The patient is a female approximately 40 years of age · a dermatoscopic image of a skin lesion:
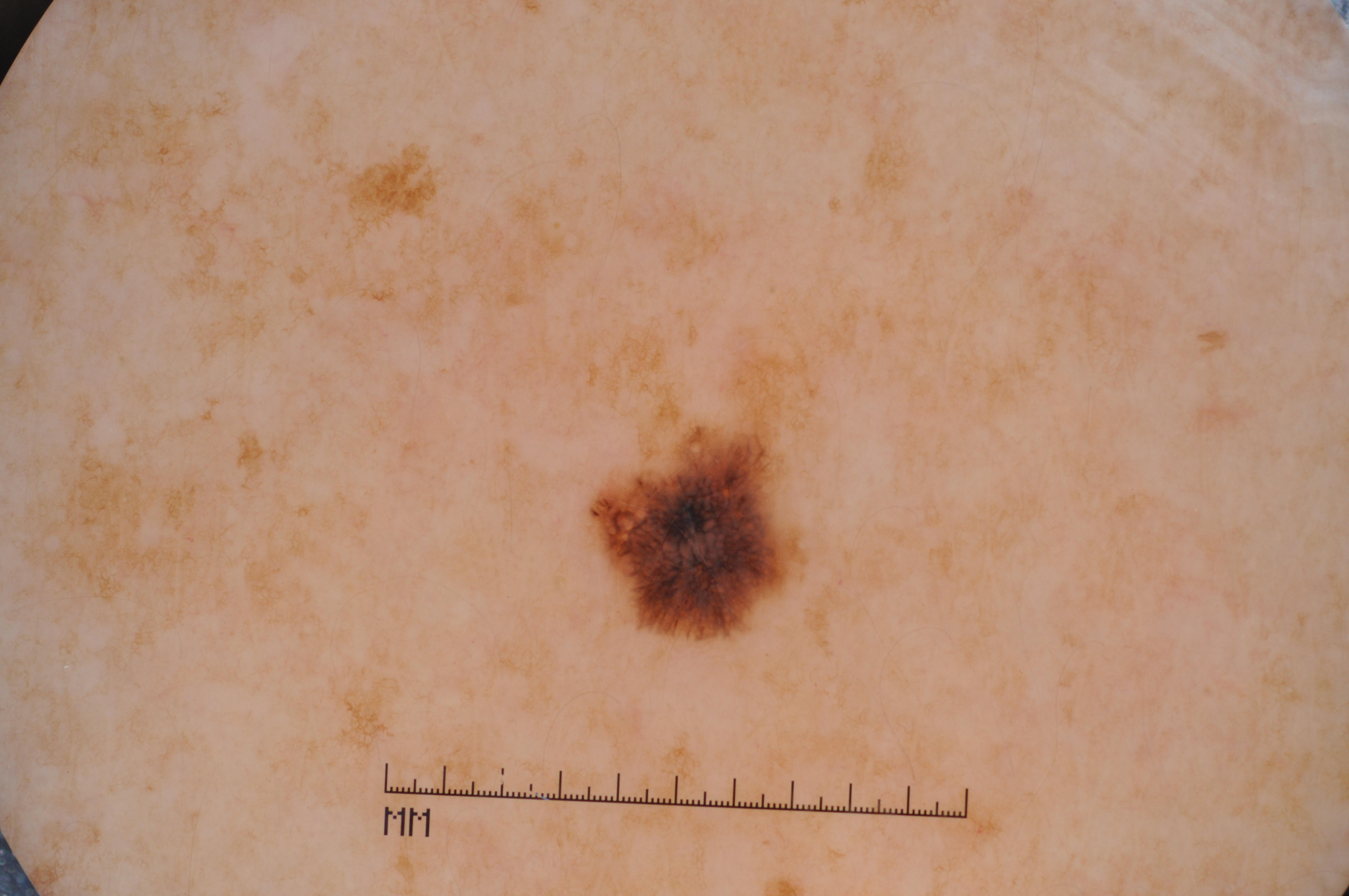Findings: Dermoscopic assessment notes pigment network. The lesion spans (590, 427, 801, 637). Impression: The clinical diagnosis was a melanocytic nevus.